A patient age 41:
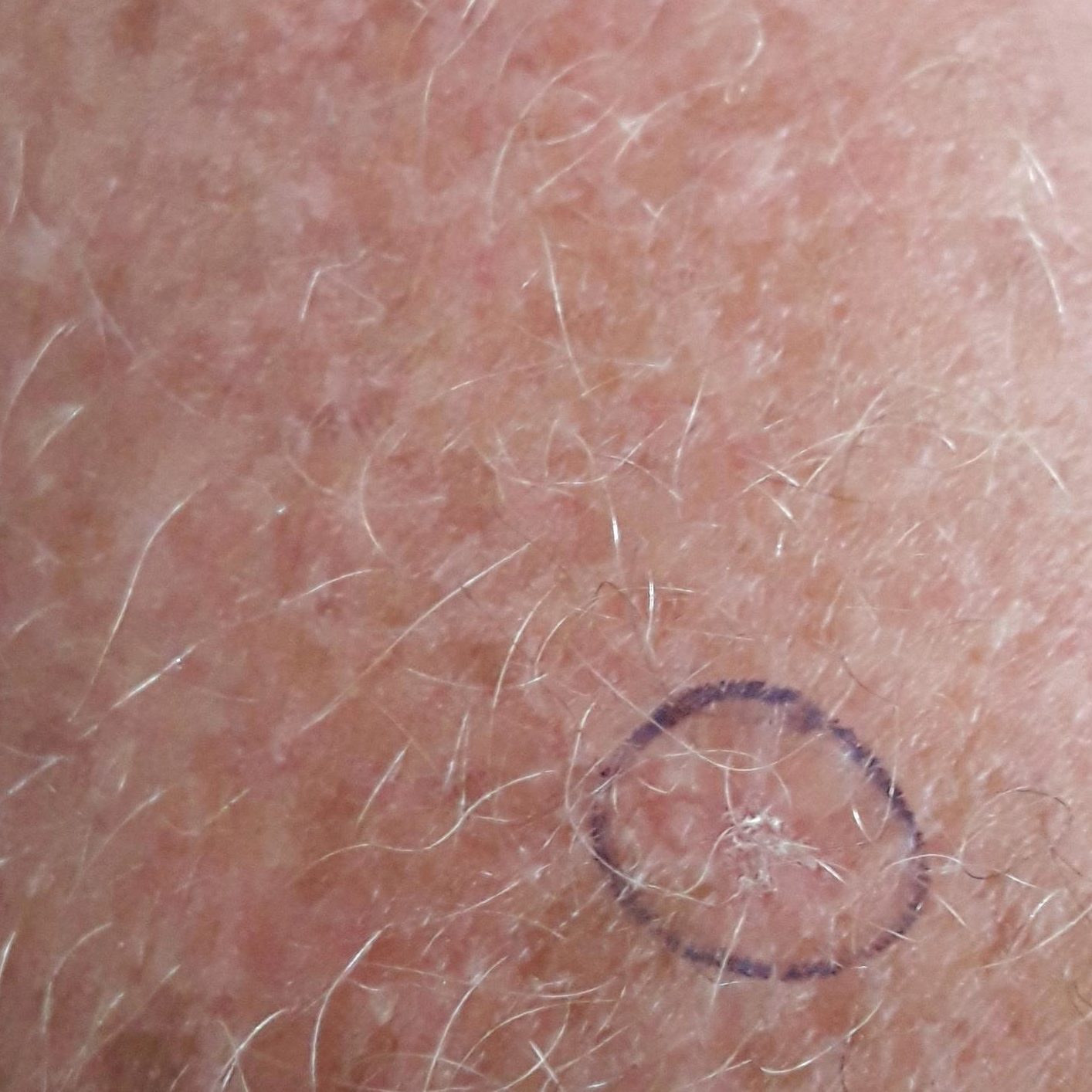region = a forearm | diagnosis = actinic keratosis (clinical consensus).